A skin lesion imaged with a dermatoscope.
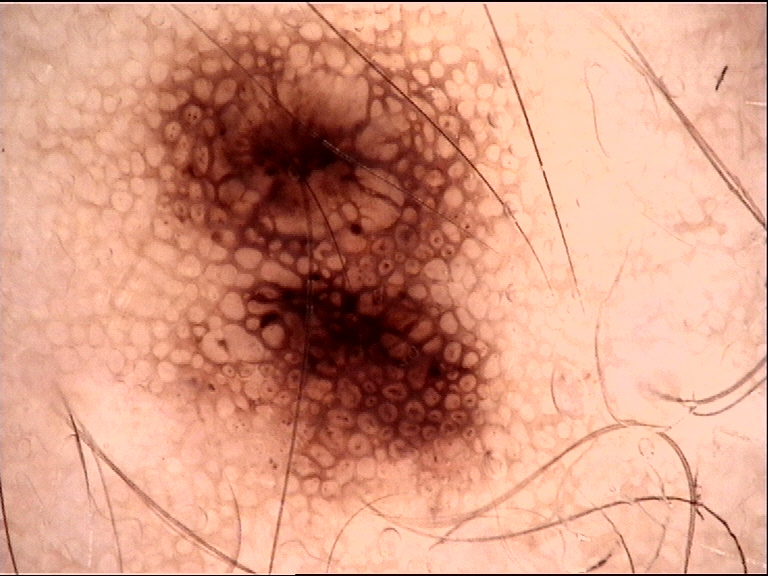Classified as a dysplastic junctional nevus.